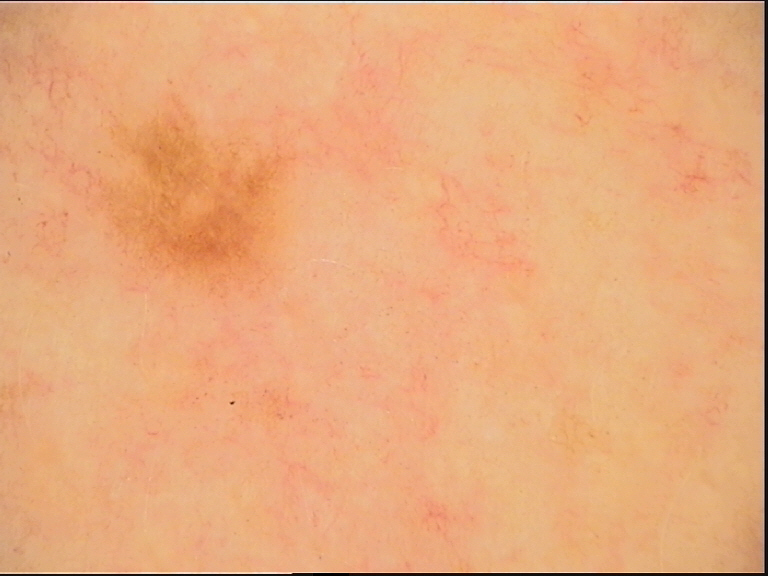| field | value |
|---|---|
| imaging | dermatoscopy |
| label | dysplastic junctional nevus (expert consensus) |